The lesion is associated with enlargement, itching, burning and bothersome appearance. No associated systemic symptoms reported. Located on the arm. Skin tone: Fitzpatrick skin type I; lay reviewers estimated Monk skin tone scale 2 or 3. Female subject, age 30–39. Close-up view.
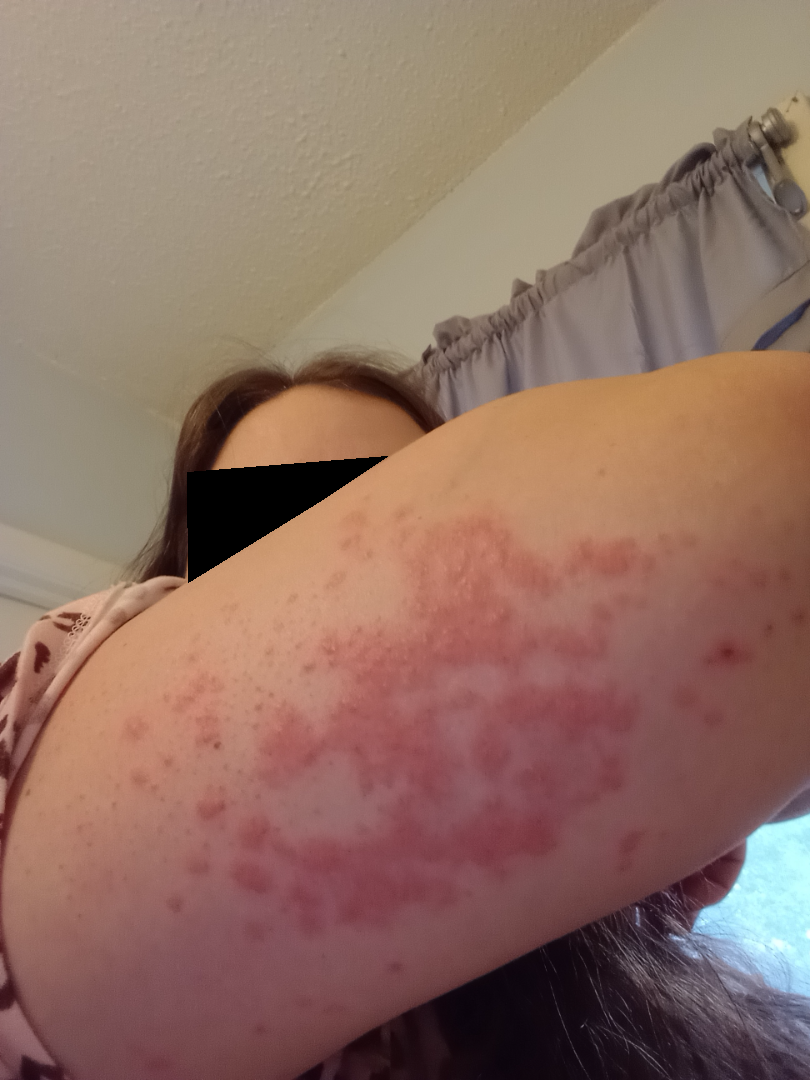Findings:
The differential is split between Eczema and Allergic Contact Dermatitis.